A skin lesion imaged with a dermatoscope.
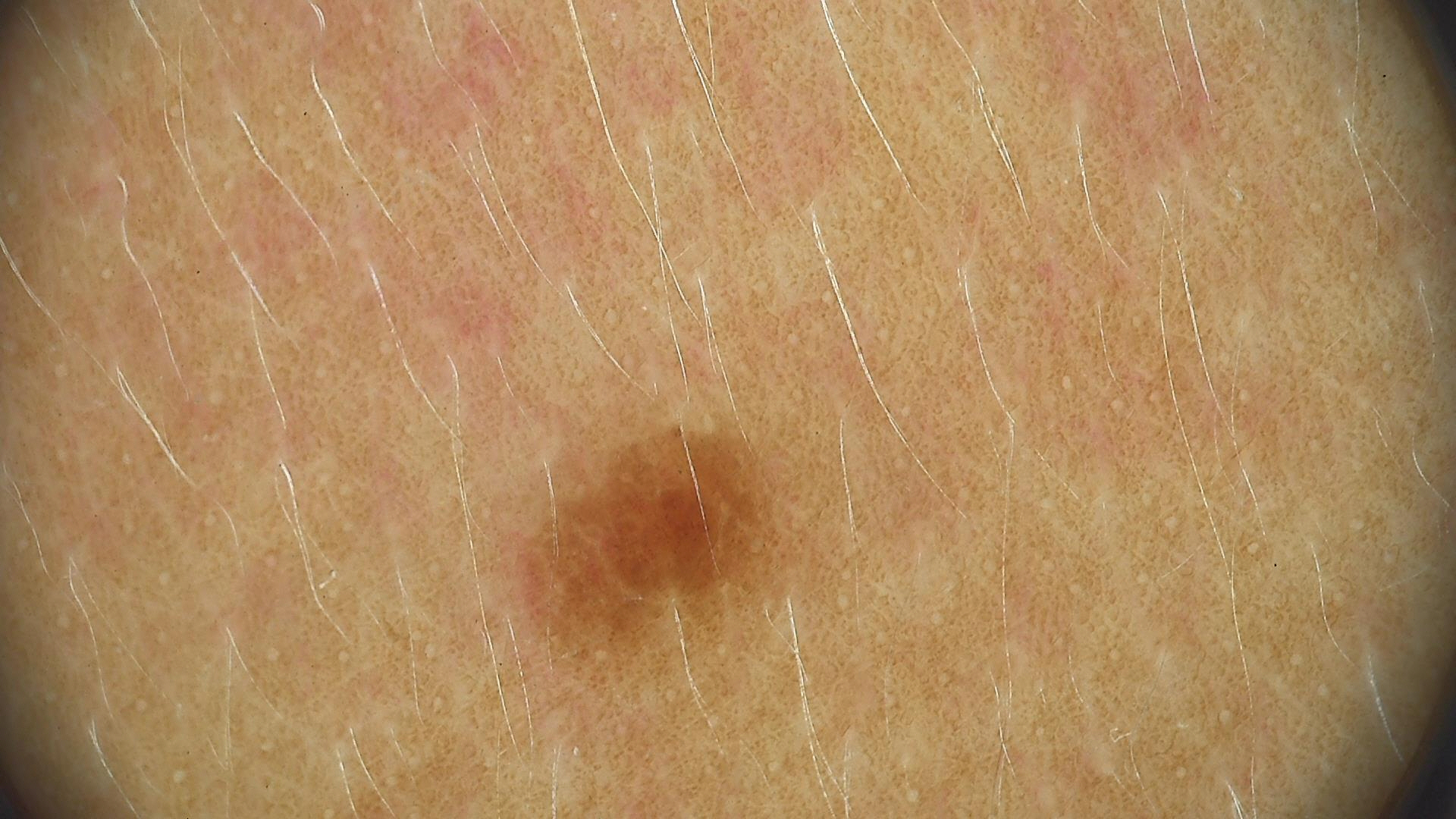Q: What kind of lesion is this?
A: banal
Q: What is the diagnosis?
A: junctional nevus (expert consensus)